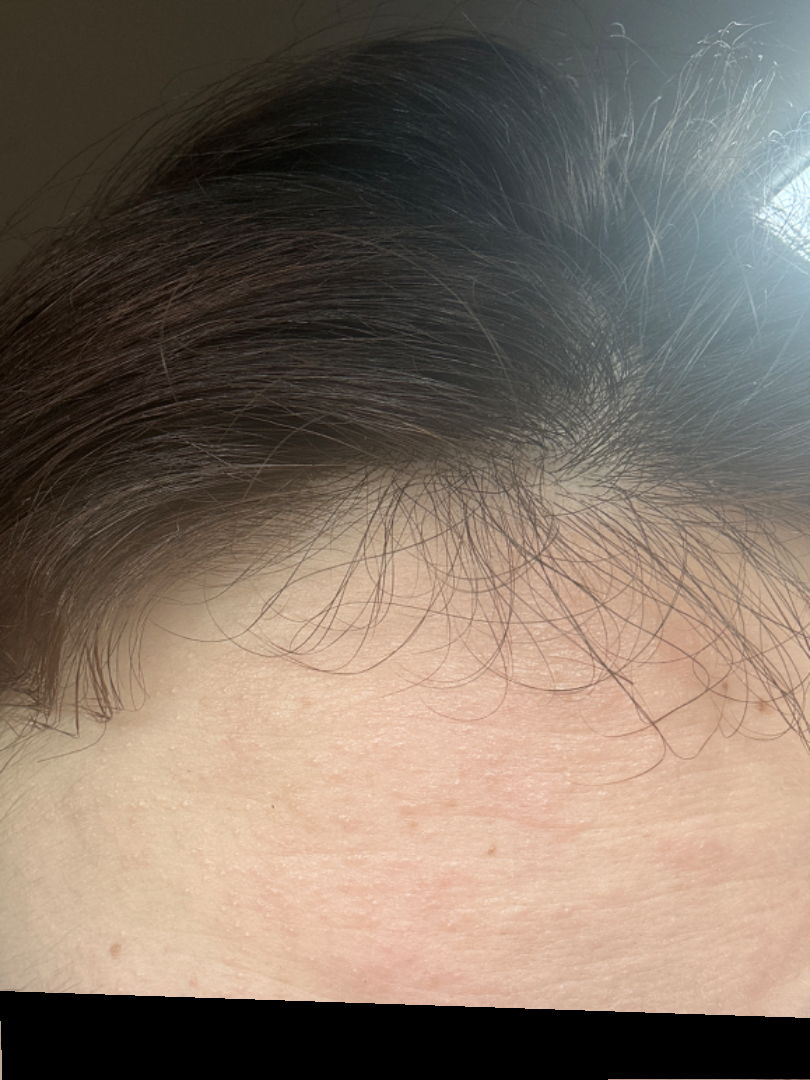The skin findings could not be characterized from the image.